The photo was captured at a distance · the patient is male · the leg is involved:
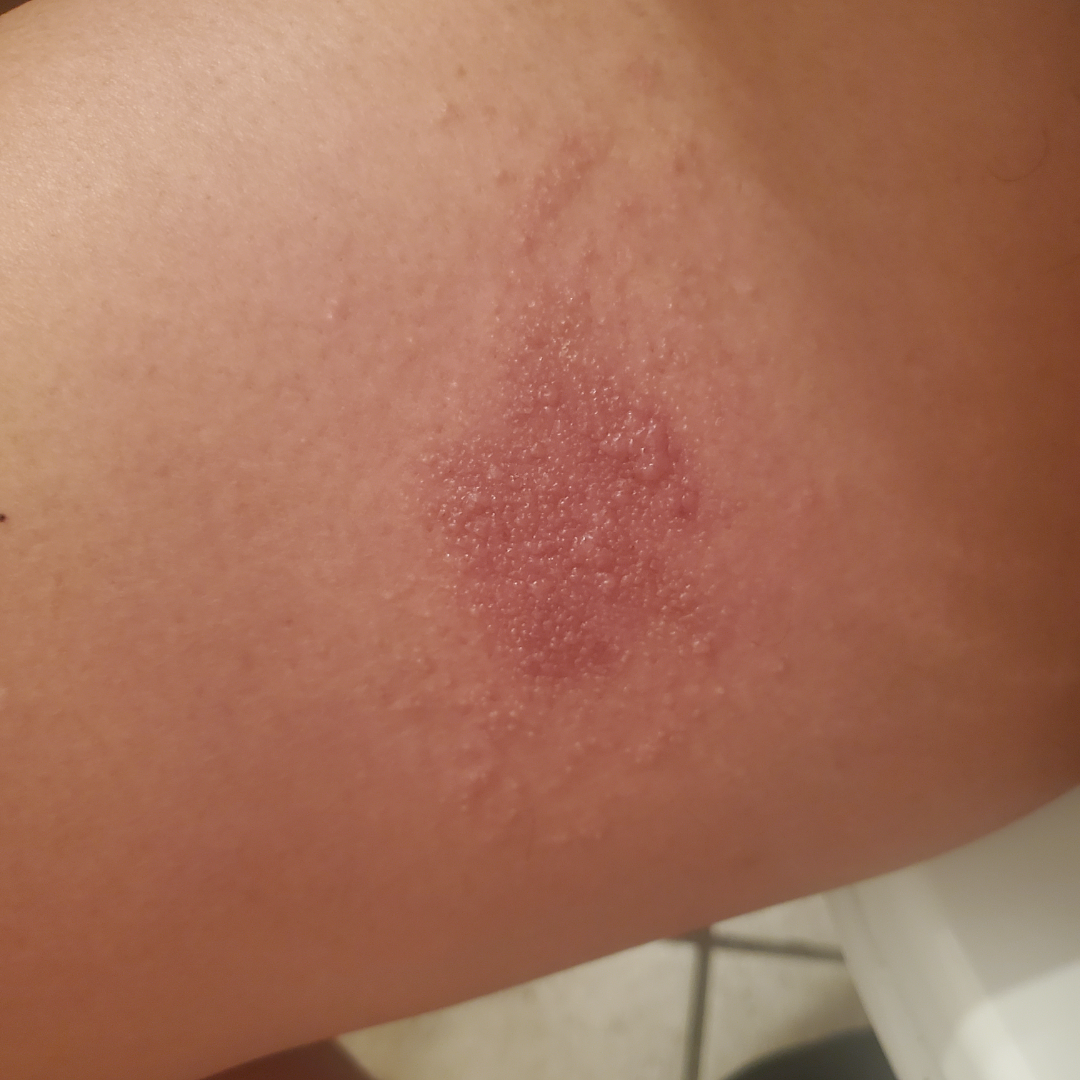| key | value |
|---|---|
| surface texture | raised or bumpy |
| patient describes the issue as | a rash |
| assessment | Allergic Contact Dermatitis (weight 0.53); Herpes Simplex (weight 0.16); Eczema (weight 0.15); Impetigo (weight 0.08); Herpes Zoster (weight 0.08) |